The photo was captured at a distance, present for less than one week, the arm is involved:
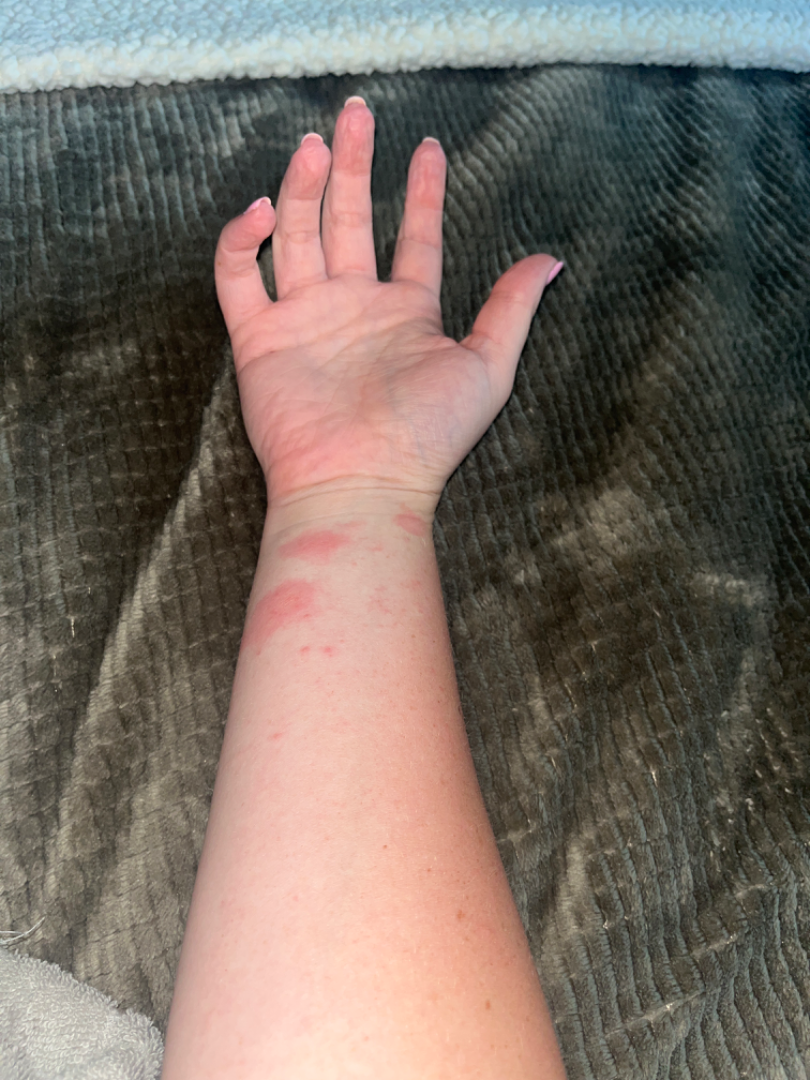Findings: Single-reviewer assessment: the leading consideration is Insect Bite; the differential also includes Urticaria; less probable is Allergic Contact Dermatitis.